Close-up view:
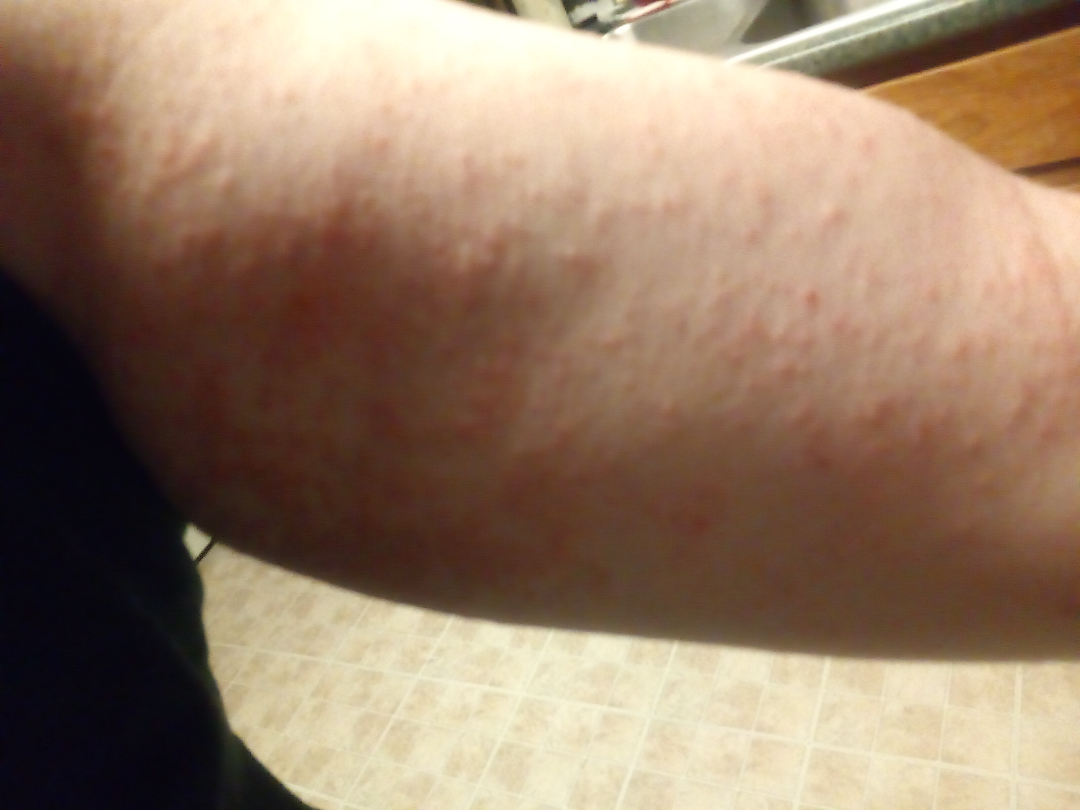A single dermatologist reviewed the case: Viral Exanthem and Drug Rash were considered with similar weight; less probable is Hypersensitivity.